Dermoscopy of a skin lesion, the subject is female: 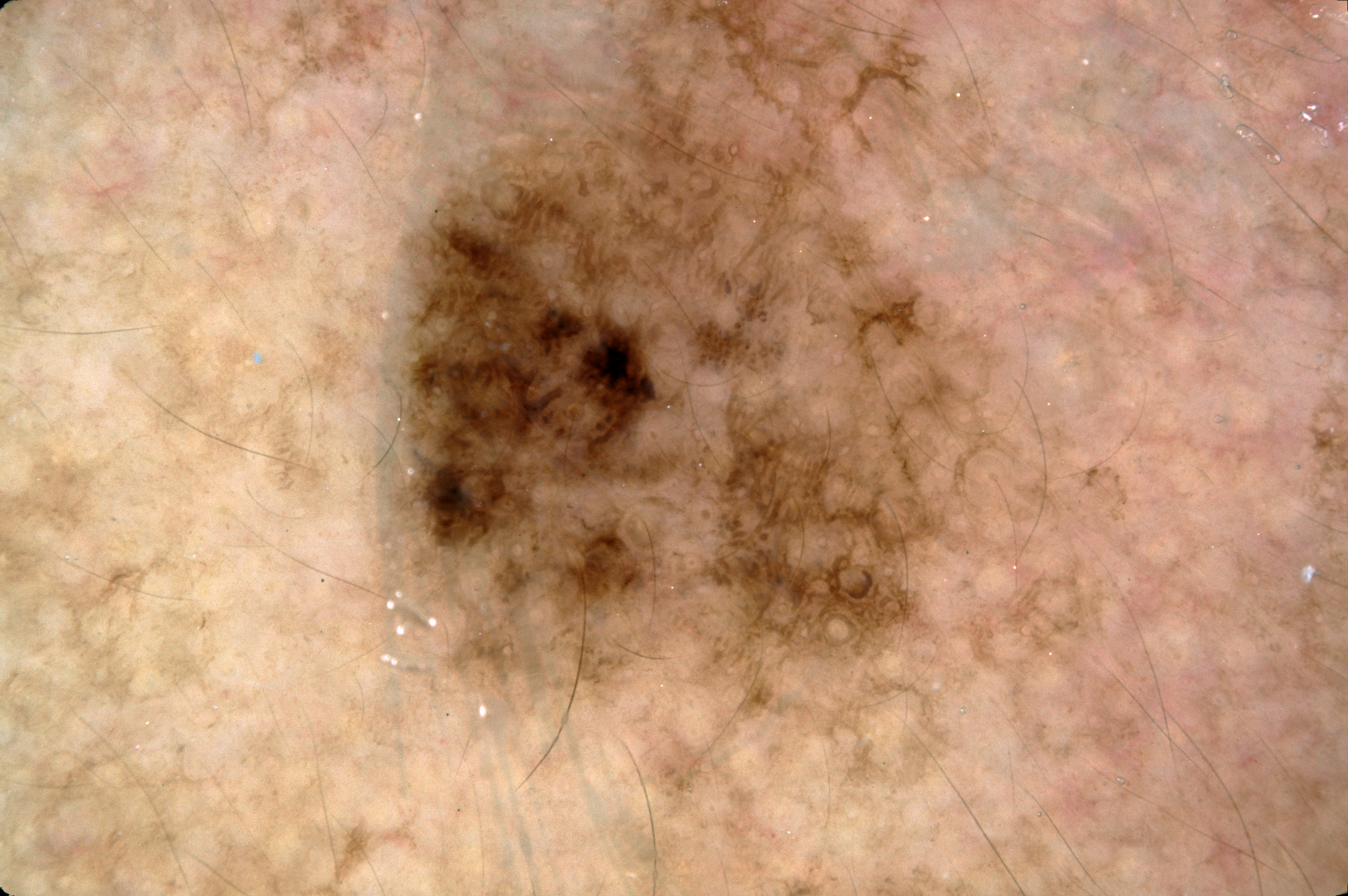extent — large | lesion location — box(337, 1, 1176, 847) | features — pigment network; absent: streaks, milia-like cysts, and negative network | assessment — a melanocytic nevus, a benign lesion.